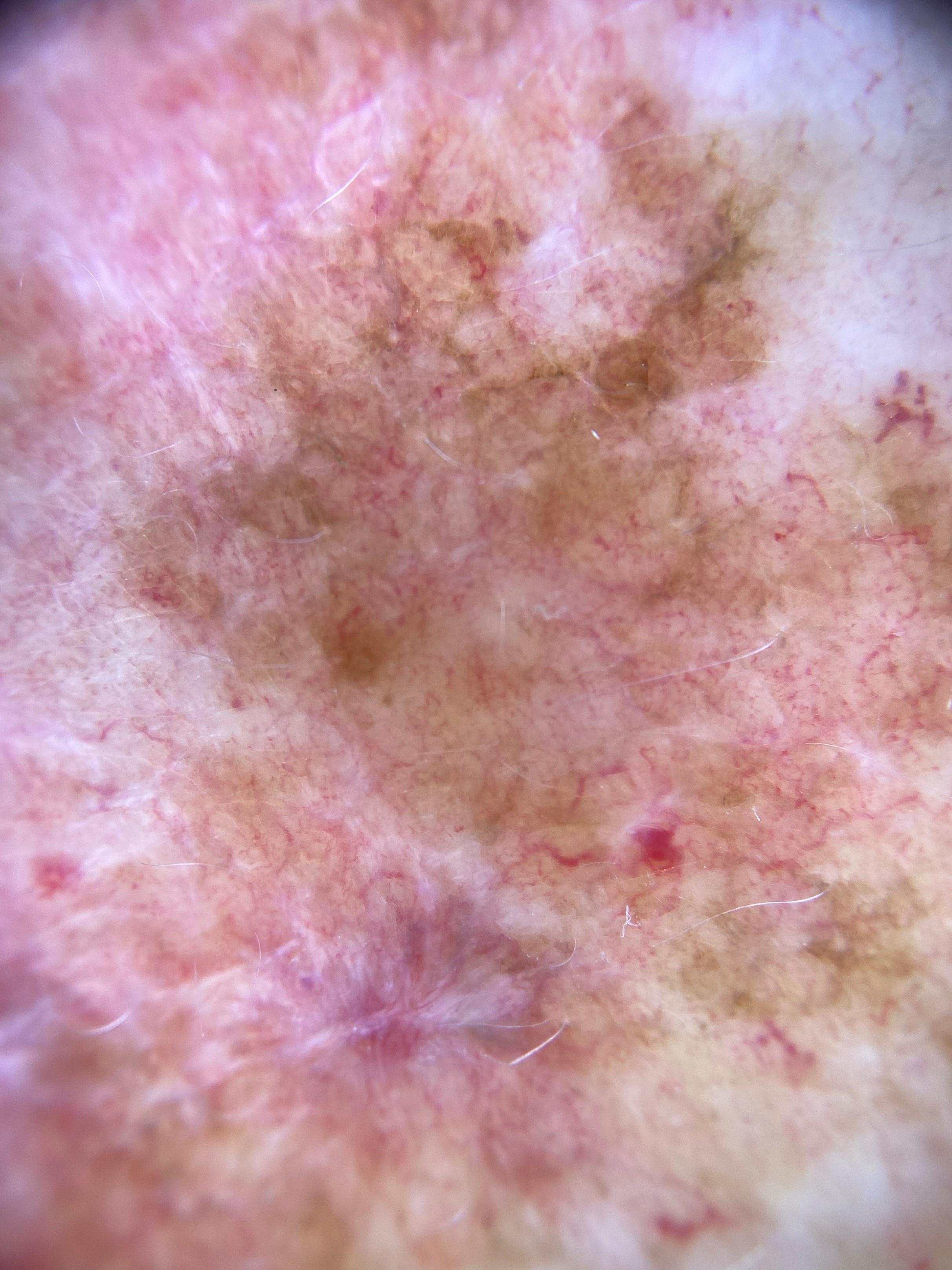Contact-polarized dermoscopy of a skin lesion.
Located on an upper extremity.
Biopsy-confirmed as a melanoma.